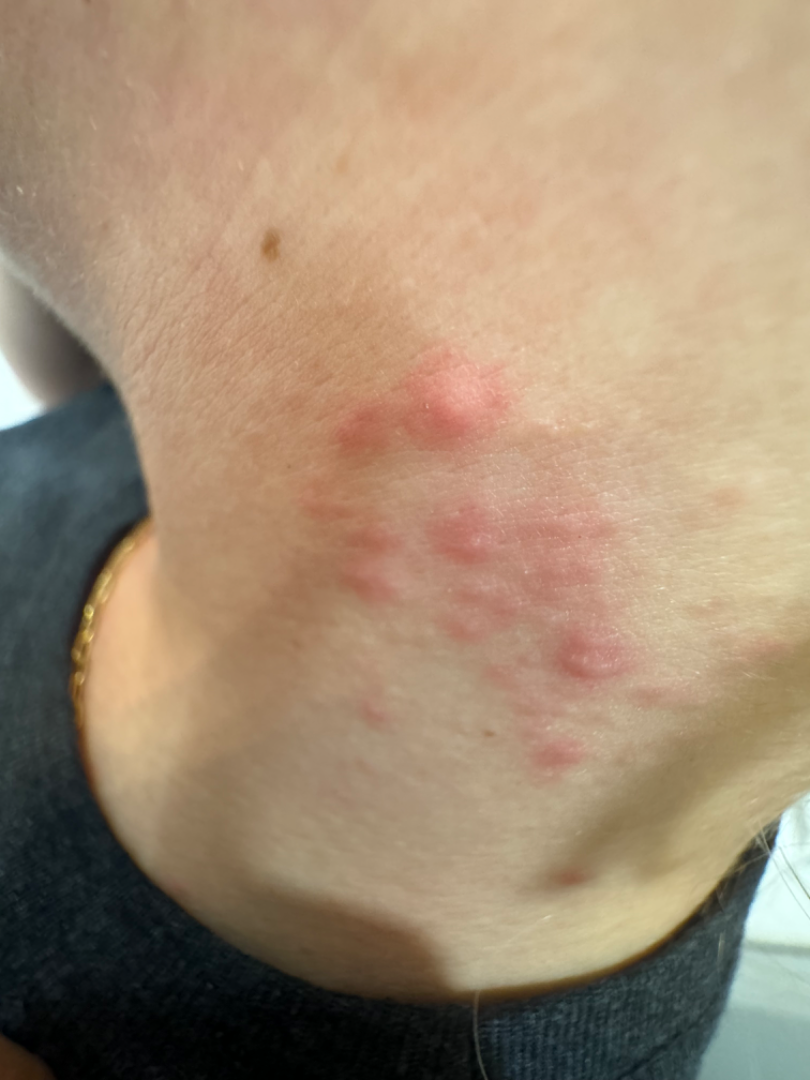Clinical context:
The patient reports bothersome appearance. This is a close-up image. Skin tone: human graders estimated Monk Skin Tone 2–3. The subject is 18–29, female. Texture is reported as fluid-filled and raised or bumpy. The lesion involves the head or neck. The patient considered this a rash.
Assessment:
On remote review of the image, Herpes Zoster, Allergic Contact Dermatitis and Herpes Simplex were considered with similar weight.